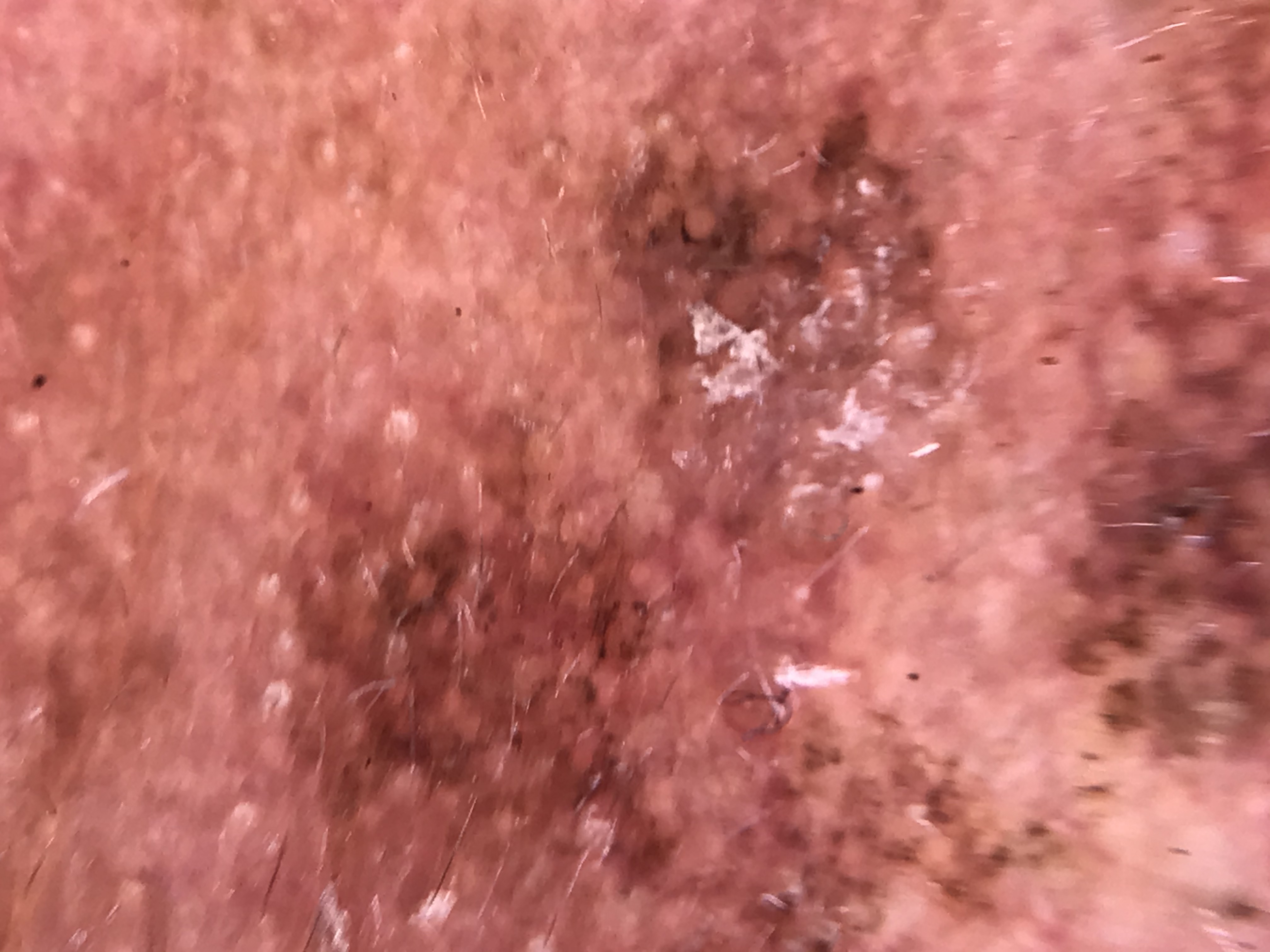classification — keratinocytic
diagnostic label — actinic keratosis (expert consensus)